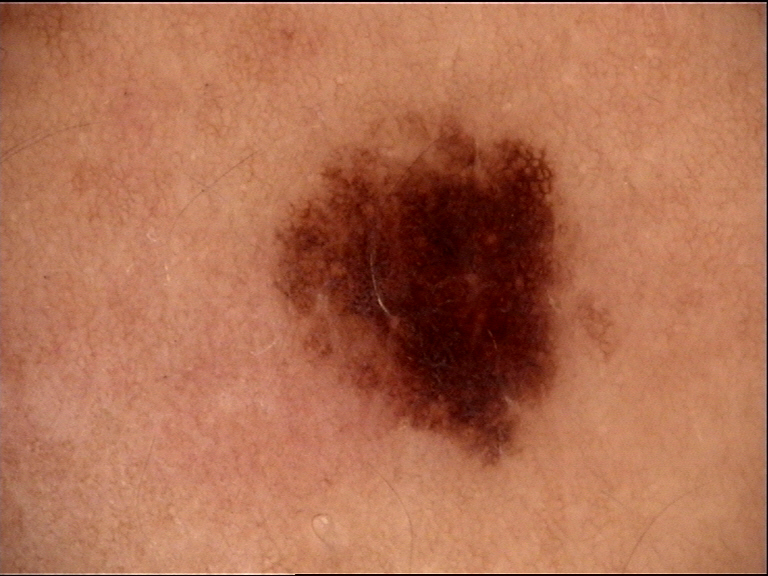Classified as a benign lesion — a dysplastic junctional nevus.